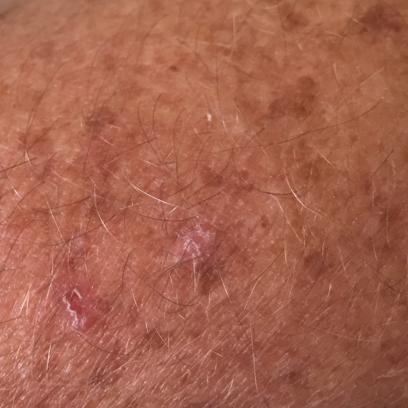Findings:
A patient 68 years of age. A clinical photo of a skin lesion taken with a smartphone. Located on a forearm. The patient describes that the lesion itches.
Impression:
Expert review favored an actinic keratosis.